Located on the leg, arm and head or neck. A close-up photograph:
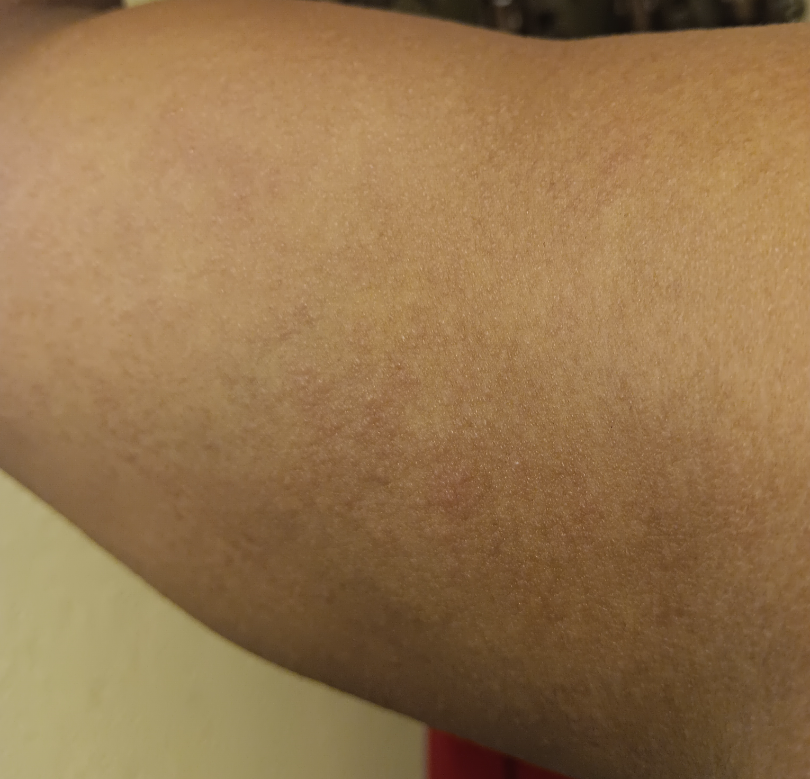The dermatologist could not determine a likely condition from the photograph alone.
Self-categorized by the patient as acne.
The patient indicates burning and itching.
Skin tone: Fitzpatrick skin type V.
The condition has been present for one to four weeks.
The patient indicates the lesion is raised or bumpy.